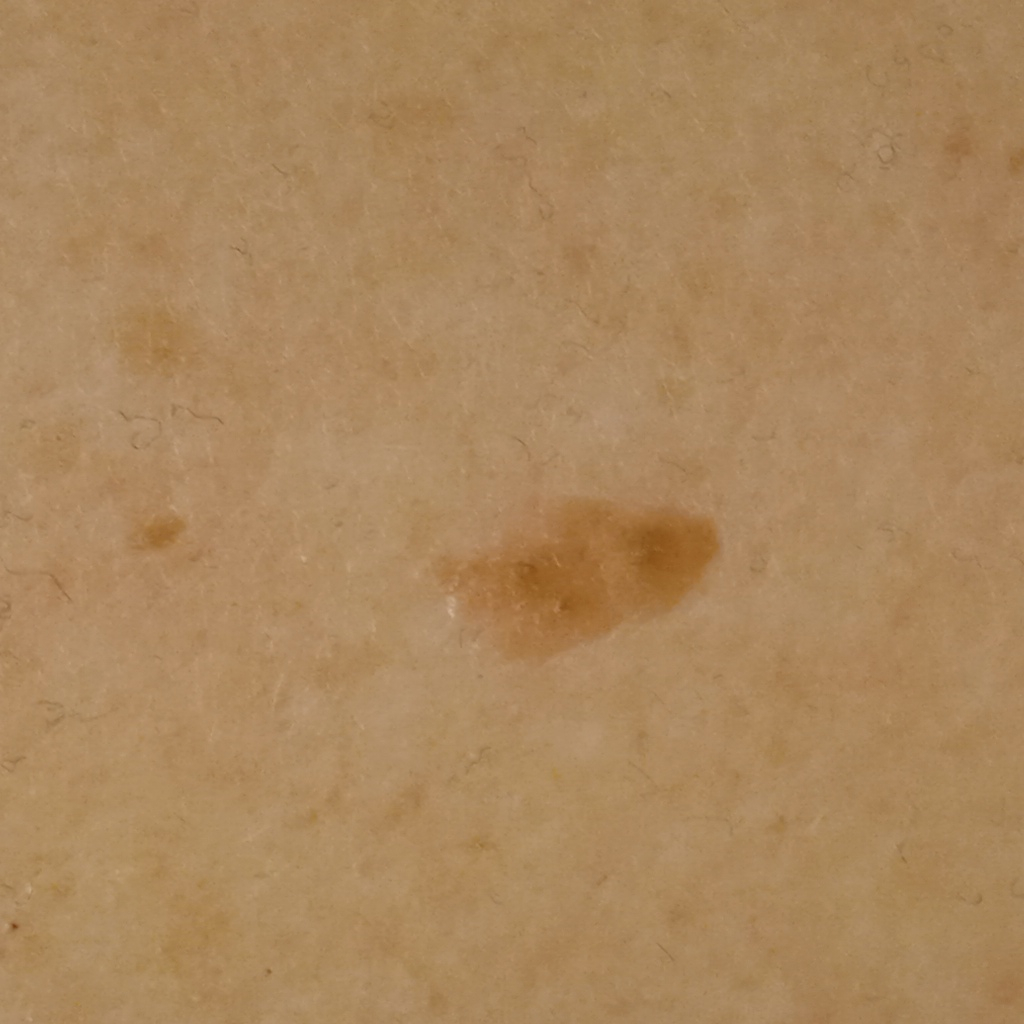Impression:
The dermatologists' assessment was a seborrheic keratosis.